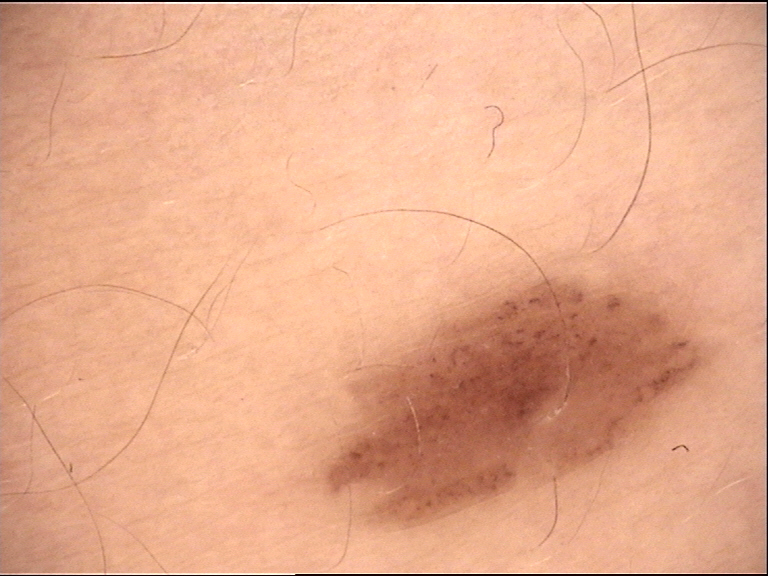Conclusion: The diagnostic label was a benign lesion — a dysplastic junctional nevus.